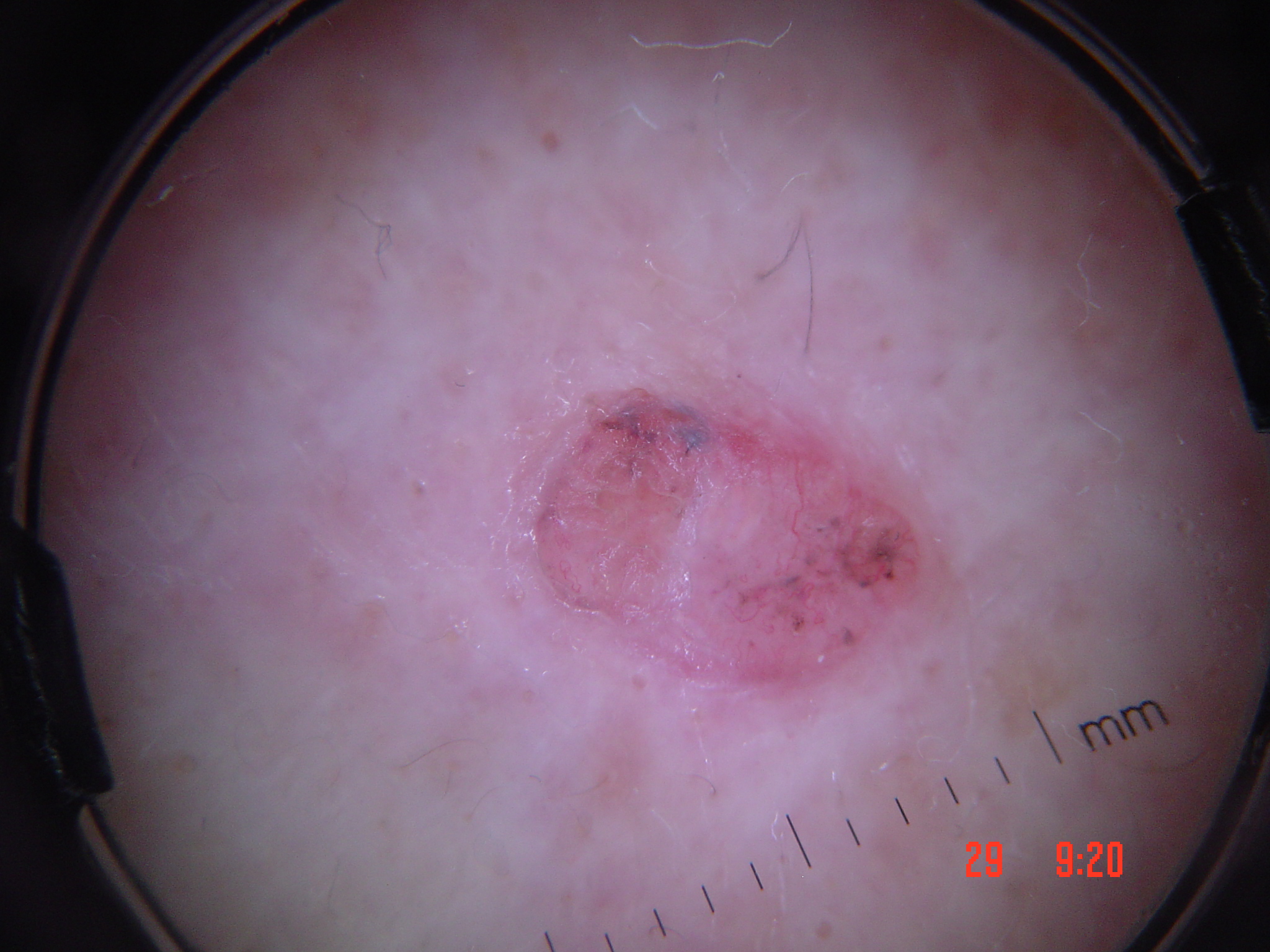The morphology is that of a keratinocytic lesion. Biopsy-confirmed as a basal cell carcinoma.